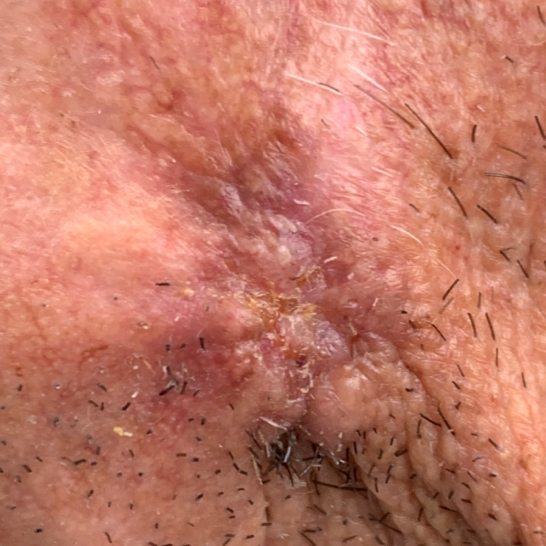imaging — smartphone clinical photo
exposure history — pesticide exposure
skin phototype — II
location — the face
lesion diameter — approx. 15 × 13 mm
pathology — squamous cell carcinoma (biopsy-proven)